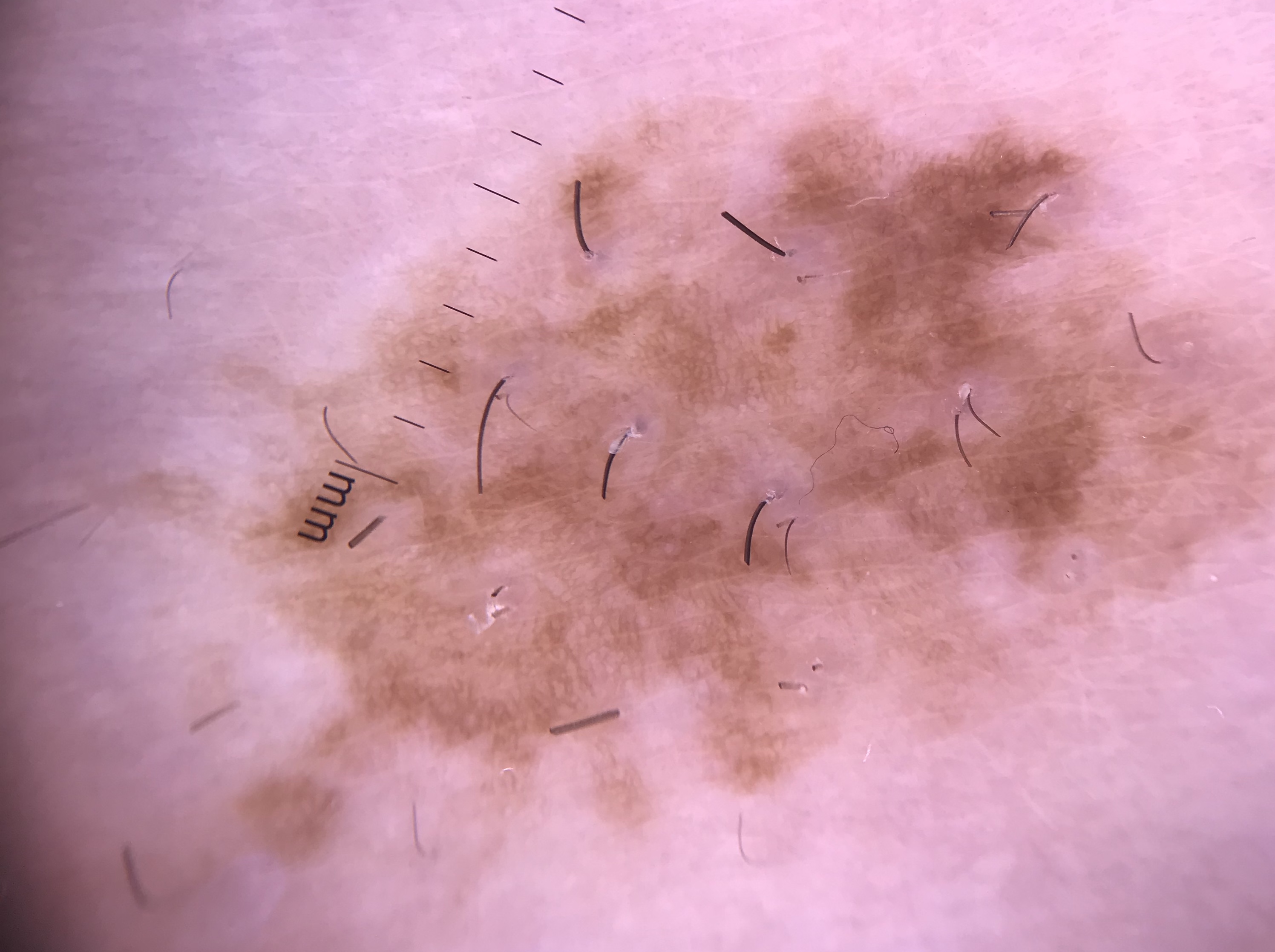Findings: The architecture is that of a banal lesion. Impression: The diagnostic label was a congenital compound nevus.